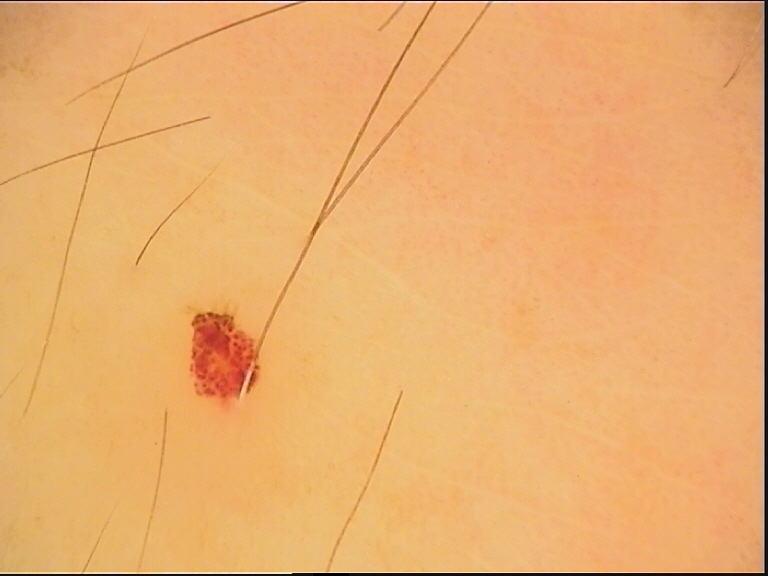Case:
– image · dermoscopy
– assessment · hemangioma (expert consensus)